Located on the top or side of the foot. The lesion is described as raised or bumpy. Present for one to three months. This is a close-up image. The patient is a female aged 40–49. The patient described the issue as a rash. The lesion is associated with bothersome appearance:
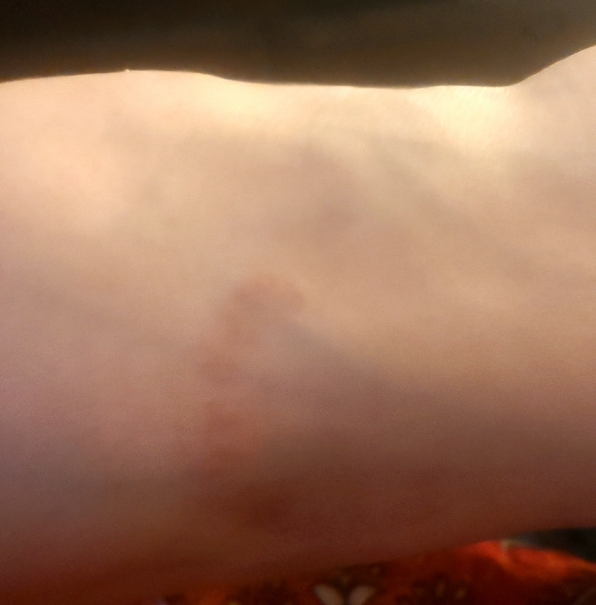Findings:
The skin condition could not be confidently assessed from this image.